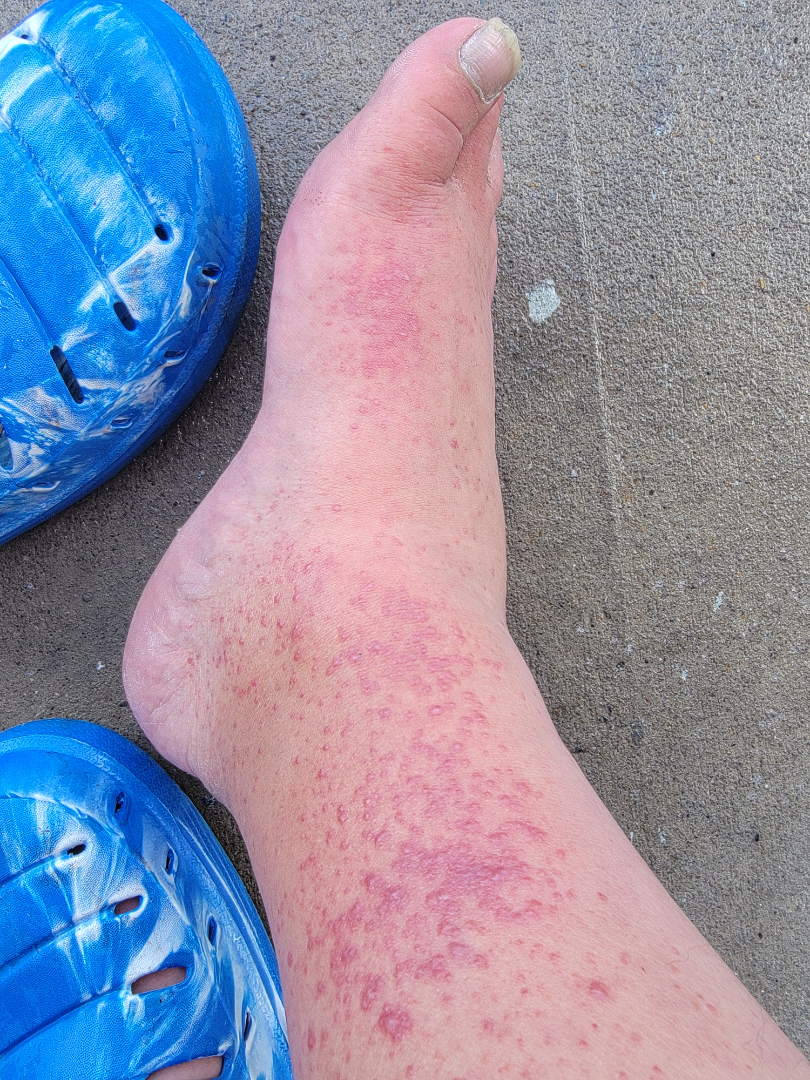On photographic review, Psoriasis (leading).